A dermatoscopic image of a skin lesion: 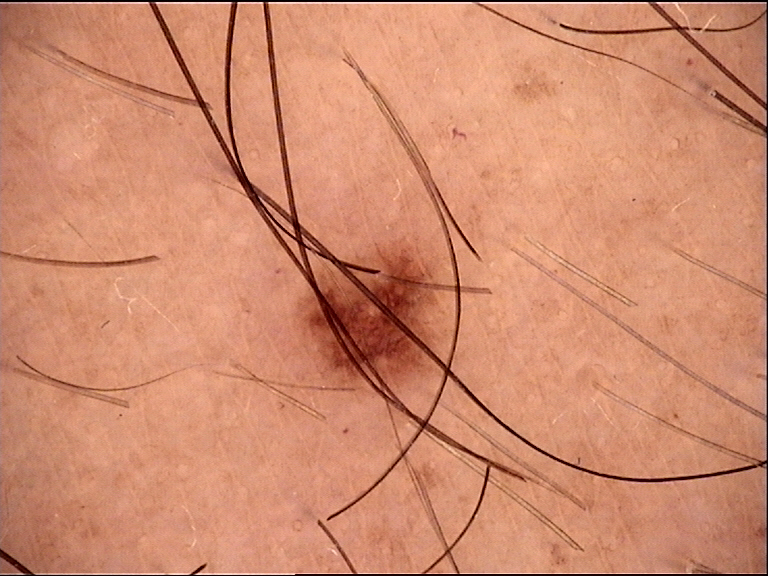diagnostic label: dysplastic junctional nevus (expert consensus).